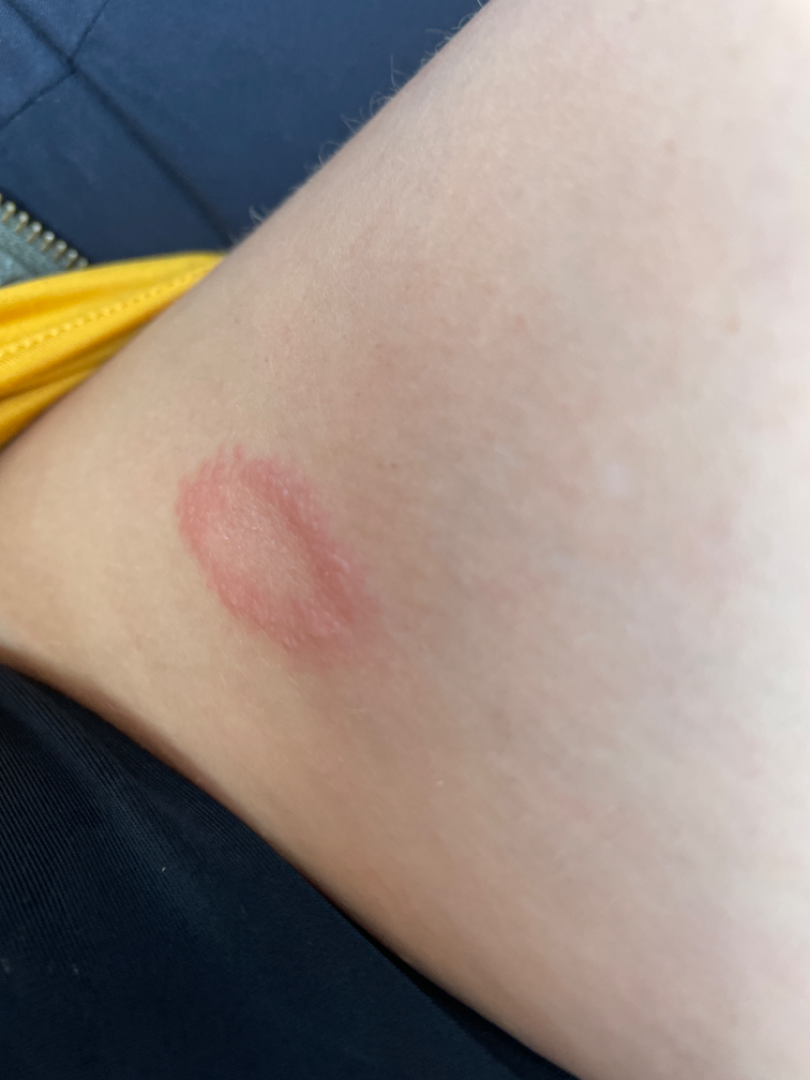The affected area is the leg. The contributor is a female aged 18–29. Self-categorized by the patient as a rash. An image taken at an angle. The patient reported no systemic symptoms. The lesion is associated with enlargement, darkening and bothersome appearance. The differential includes Pityriasis rosea and Erythema annulare centrifugum, with no clear leading consideration; less probable is Eczema; less likely is Tinea; a remote consideration is Psoriasis; lower on the differential is Granuloma annulare.